The photograph is a close-up of the affected area: 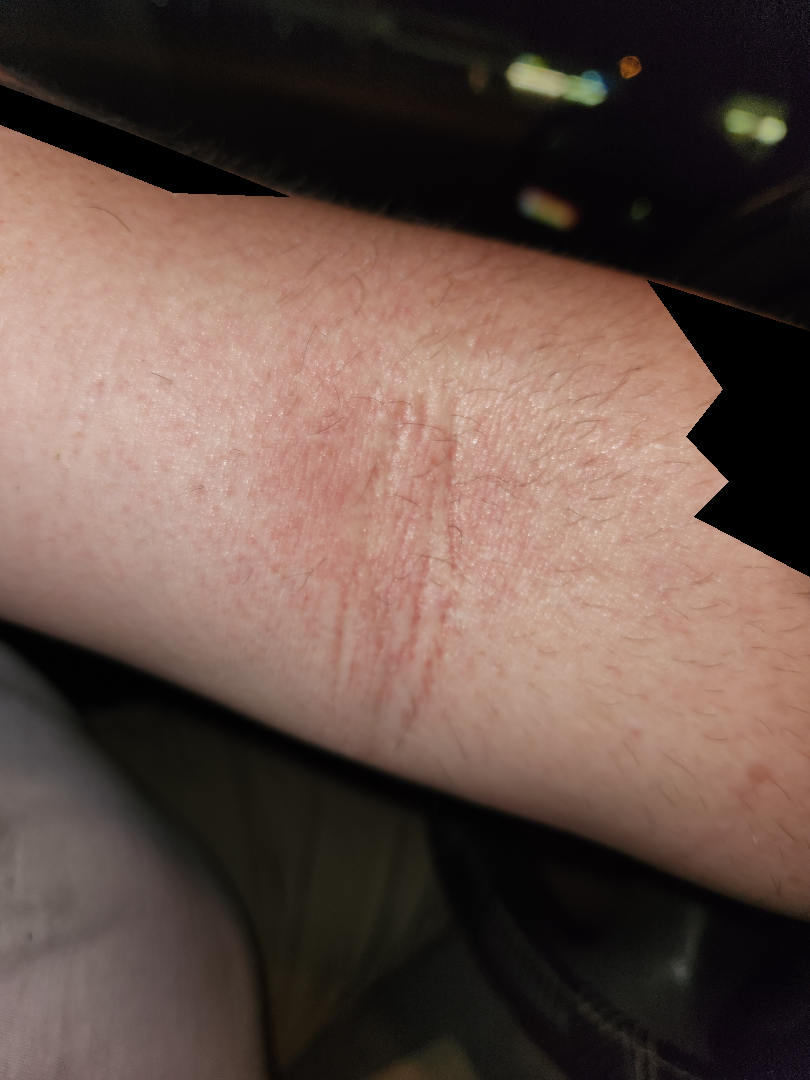Consistent with Eczema.